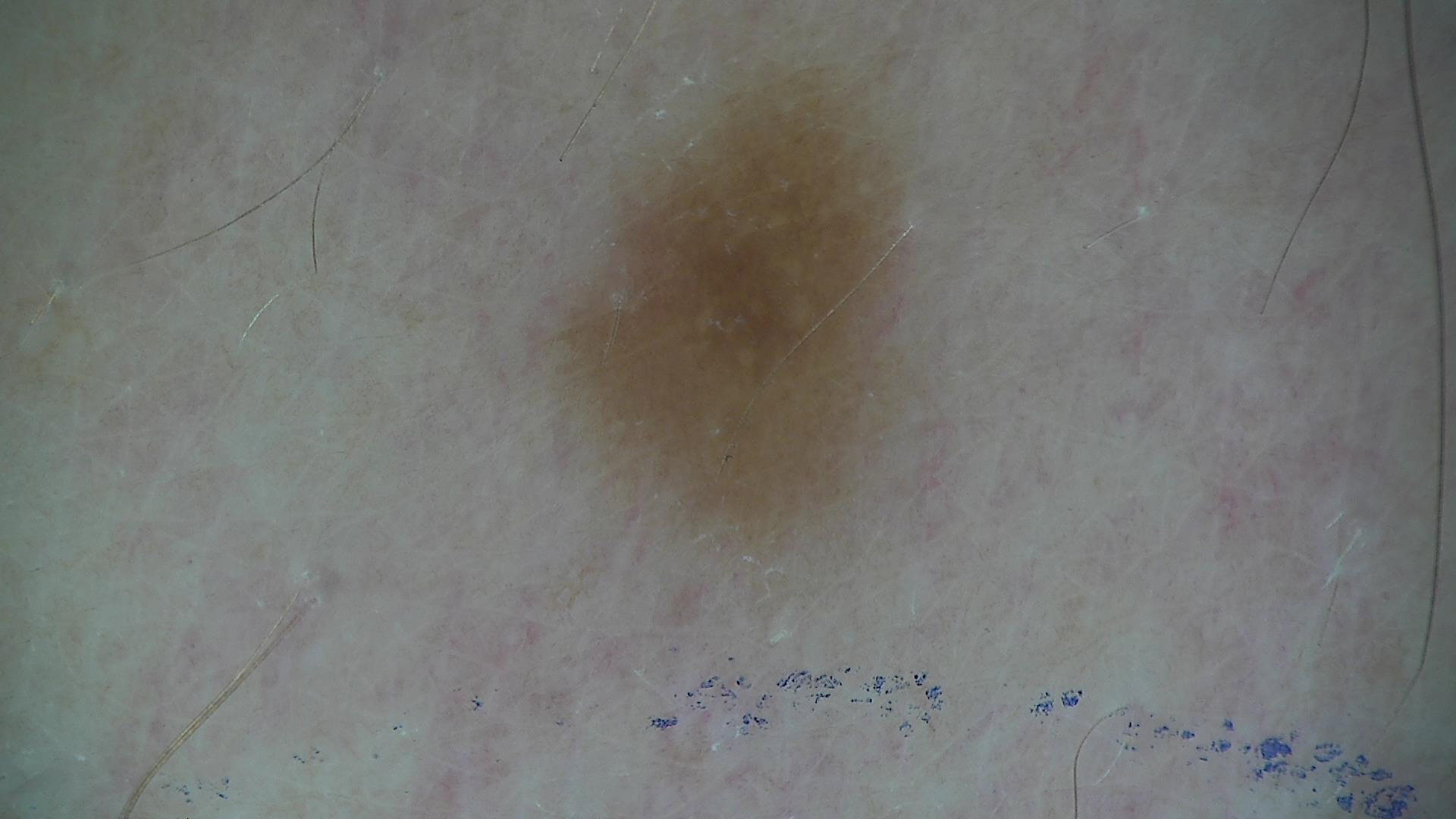Diagnosed as a banal lesion — a junctional nevus.